A dermatoscopic image of a skin lesion.
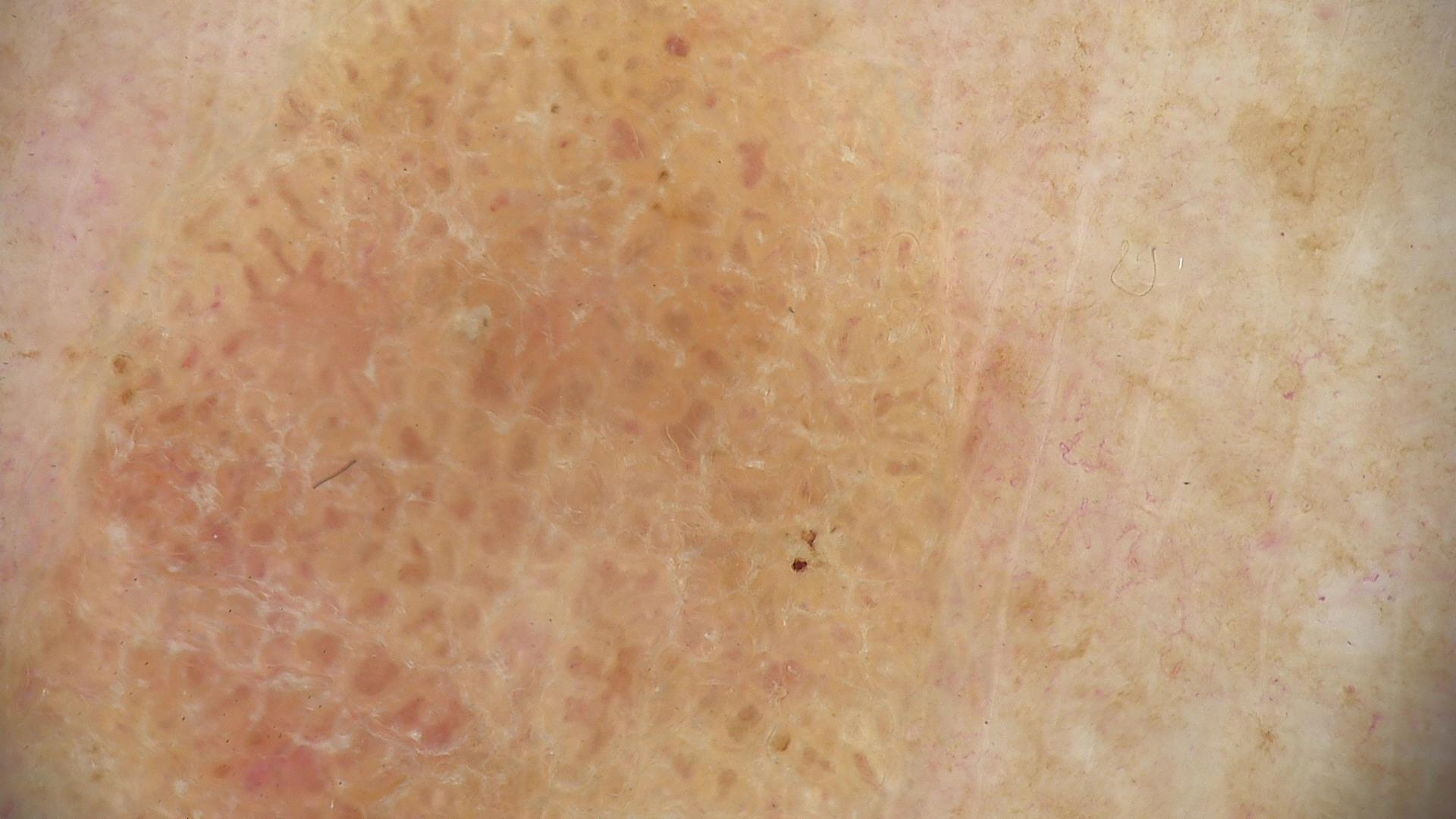category: keratinocytic
assessment: seborrheic keratosis (expert consensus)